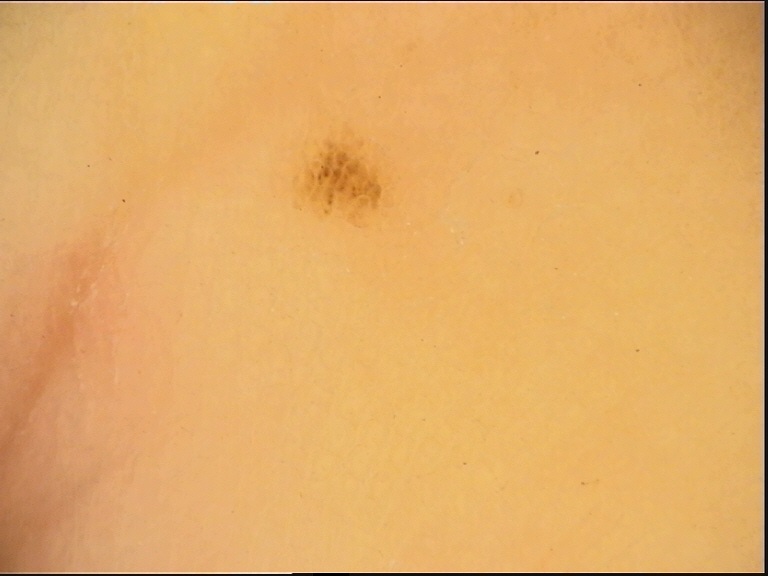image: dermoscopy
lesion_type:
  main_class: banal
  pattern: junctional
diagnosis:
  name: acral junctional nevus
  code: ajb
  malignancy: benign
  super_class: melanocytic
  confirmation: expert consensus